The referring clinician suspected basal cell carcinoma · a dermoscopy image of a skin lesion · a male patient 89 years of age: 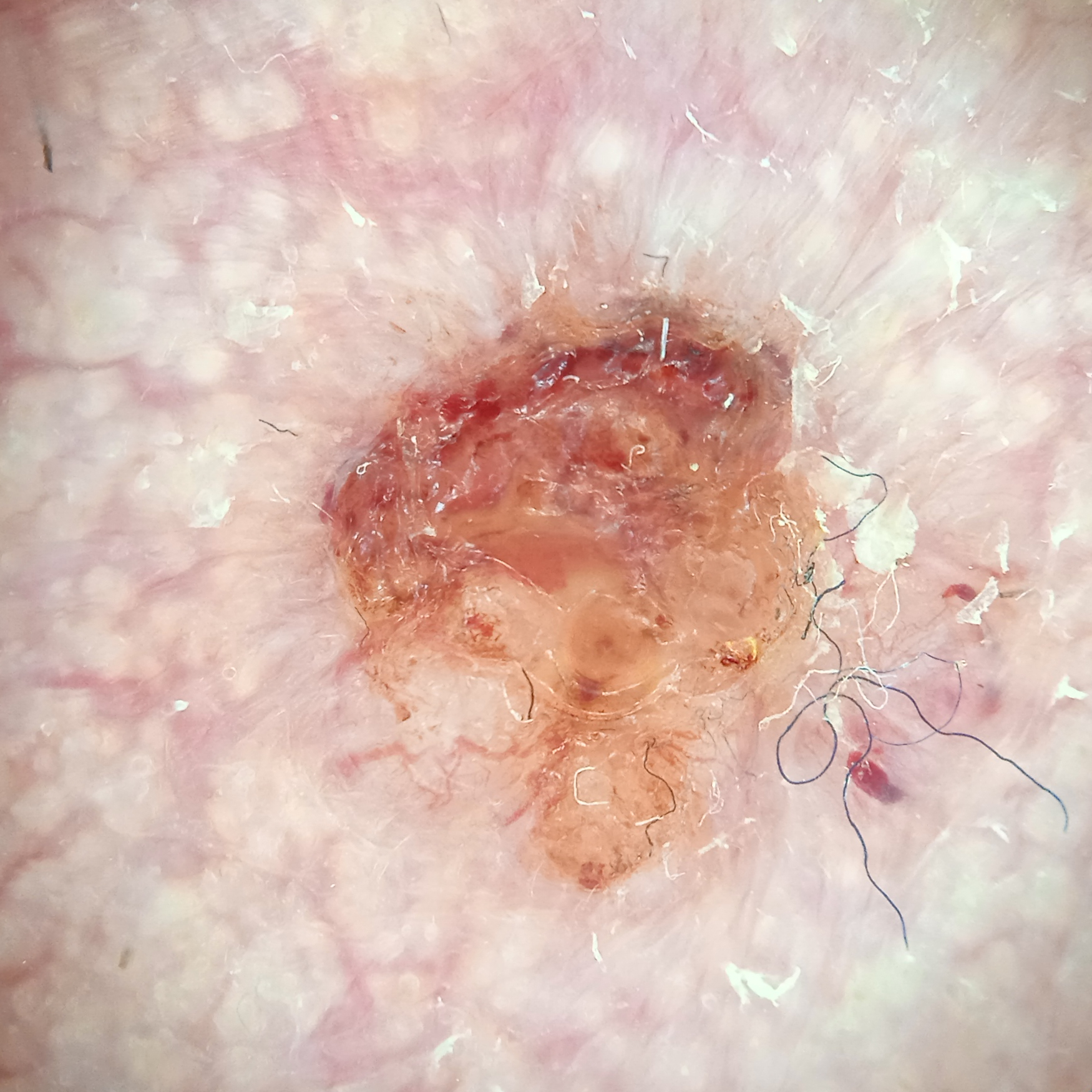The biopsy diagnosis was a basal cell carcinoma, following excision, with a measured tumor thickness of 2.2 mm.